A dermoscopic photograph of a skin lesion:
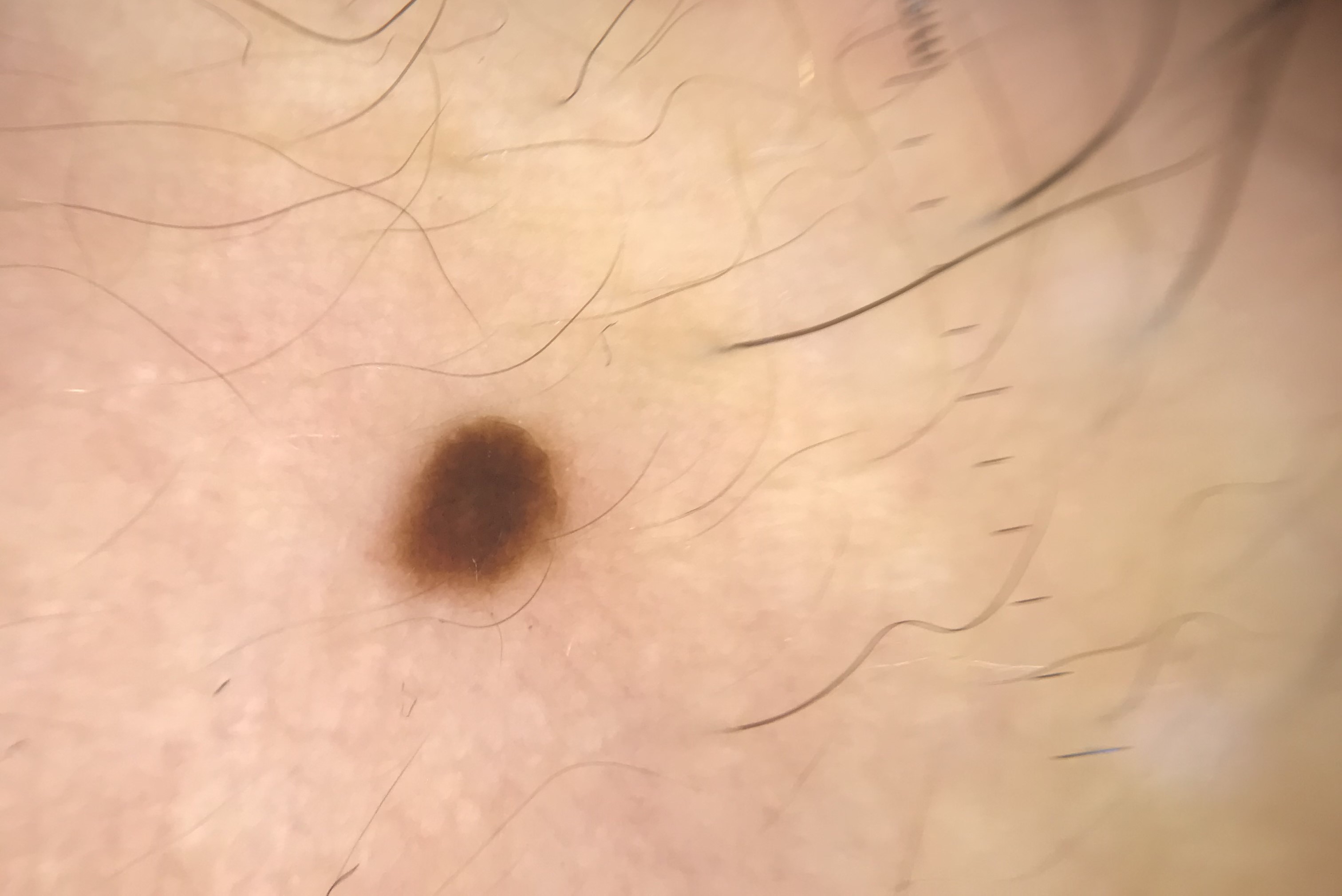{"lesion_type": {"main_class": "banal", "pattern": "junctional"}, "diagnosis": {"name": "junctional nevus", "code": "jb", "malignancy": "benign", "super_class": "melanocytic", "confirmation": "expert consensus"}}